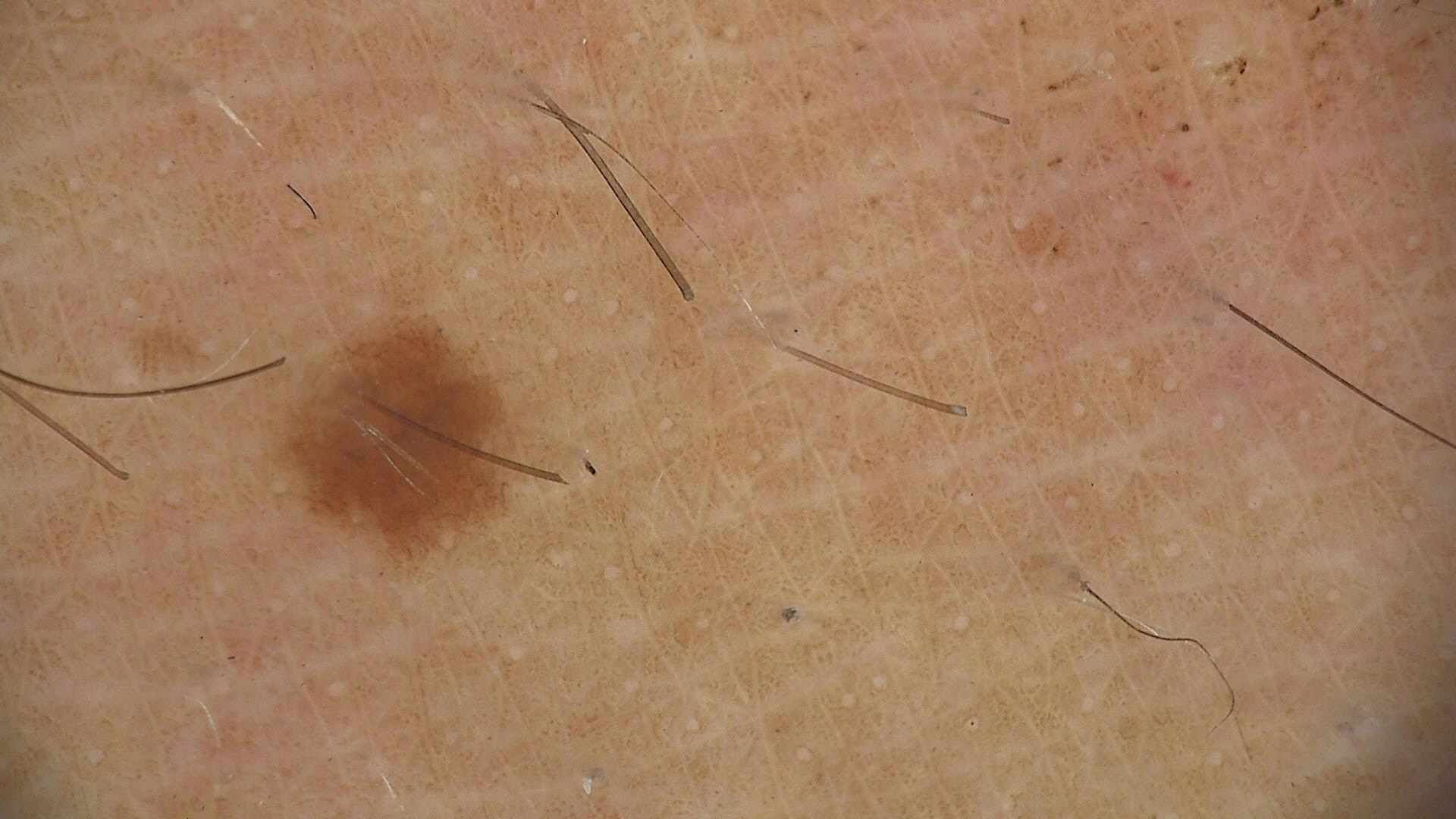Consistent with a dysplastic junctional nevus.